Skin tone: lay graders estimated Monk skin tone scale 2 · male patient, age 18–29 · symptoms reported: enlargement · the lesion involves the leg, front of the torso and arm · no relevant systemic symptoms · the photograph is a close-up of the affected area · texture is reported as raised or bumpy · present for less than one week:
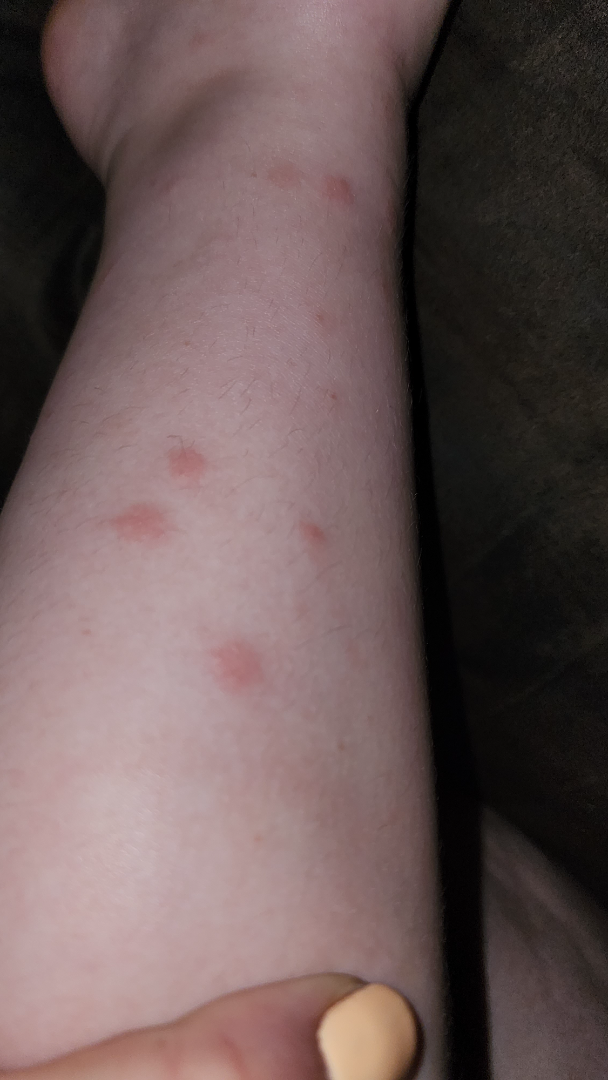Q: What is the differential diagnosis?
A: Insect Bite (100%)